Located on the arm. The photograph is a close-up of the affected area. The patient is female.
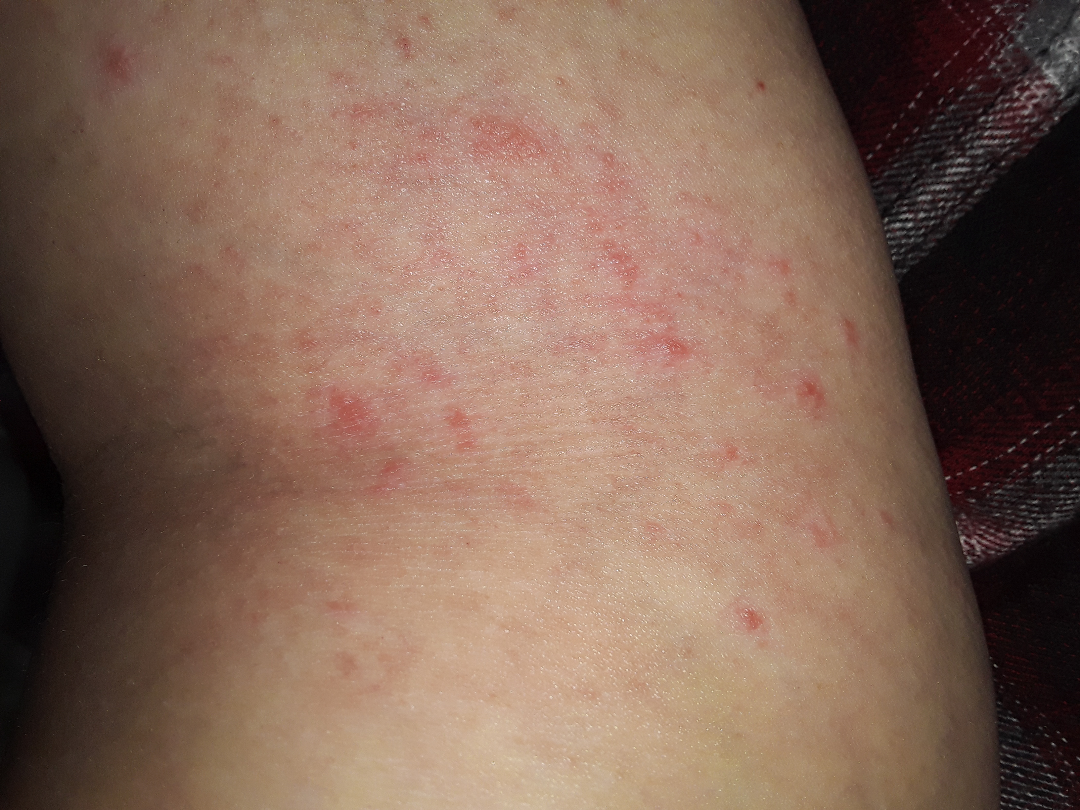Most consistent with Eczema.